Located on the leg; the contributor is male; the photograph is a close-up of the affected area:
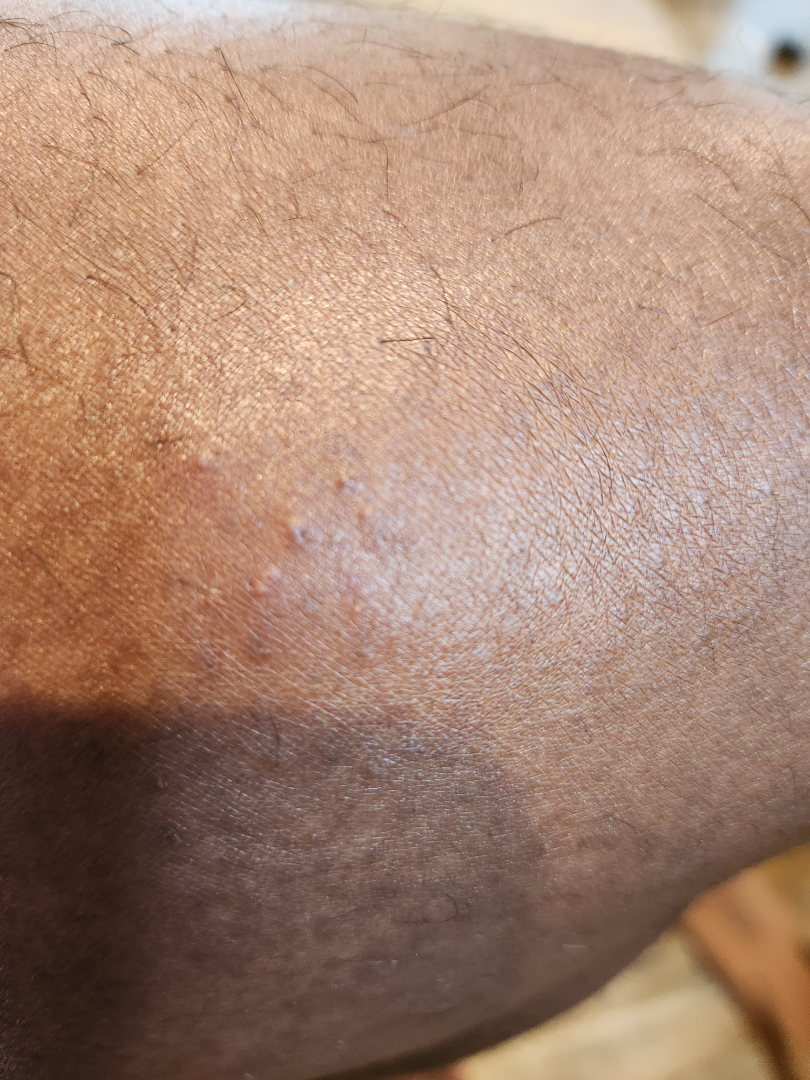skin_tone:
  fitzpatrick: V
  monk_skin_tone:
    - 4
    - 6
symptoms: itching
duration: about one day
differential:
  Eczema: 0.44
  Scabies: 0.17
  Folliculitis: 0.17
  Tinea: 0.14
  Irritant Contact Dermatitis: 0.09